A skin lesion imaged with a dermatoscope:
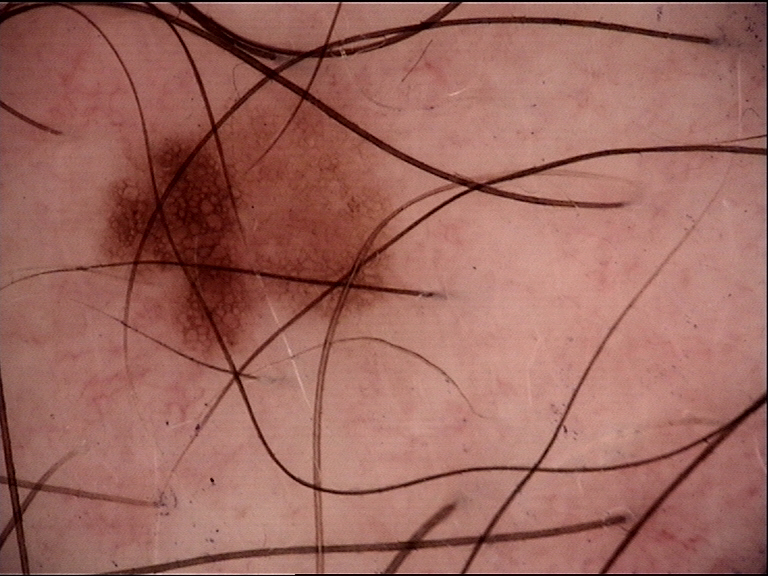Labeled as a dysplastic junctional nevus.